The lesion is described as raised or bumpy. The arm is involved. The photograph is a close-up of the affected area. The patient described the issue as a rash. The condition has been present for less than one week. Symptoms reported: itching. Female contributor, age 40–49: 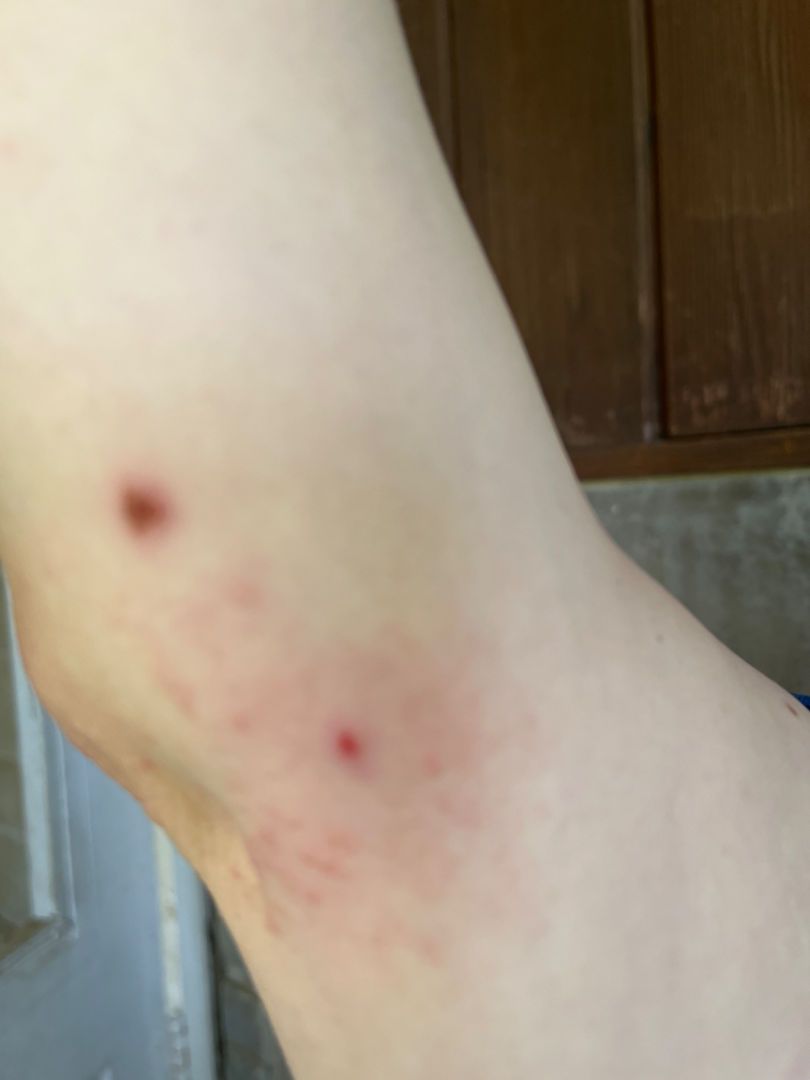Diagnostic features were not clearly distinguishable in this photograph.